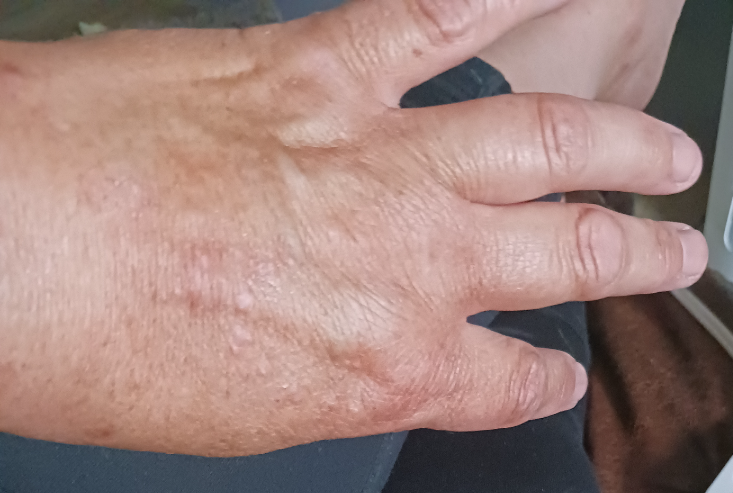The reviewing dermatologist was unable to assign a differential diagnosis from the image.